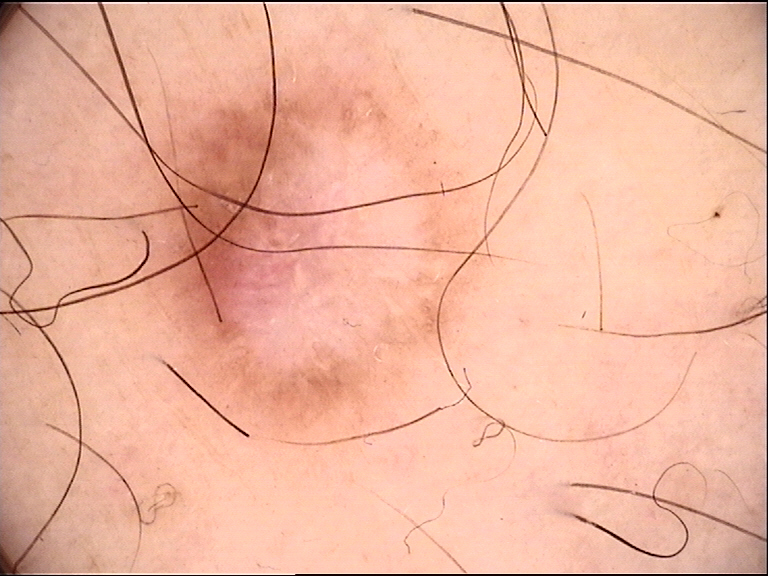modality — dermoscopy
category — fibro-histiocytic
diagnostic label — dermatofibroma (expert consensus)